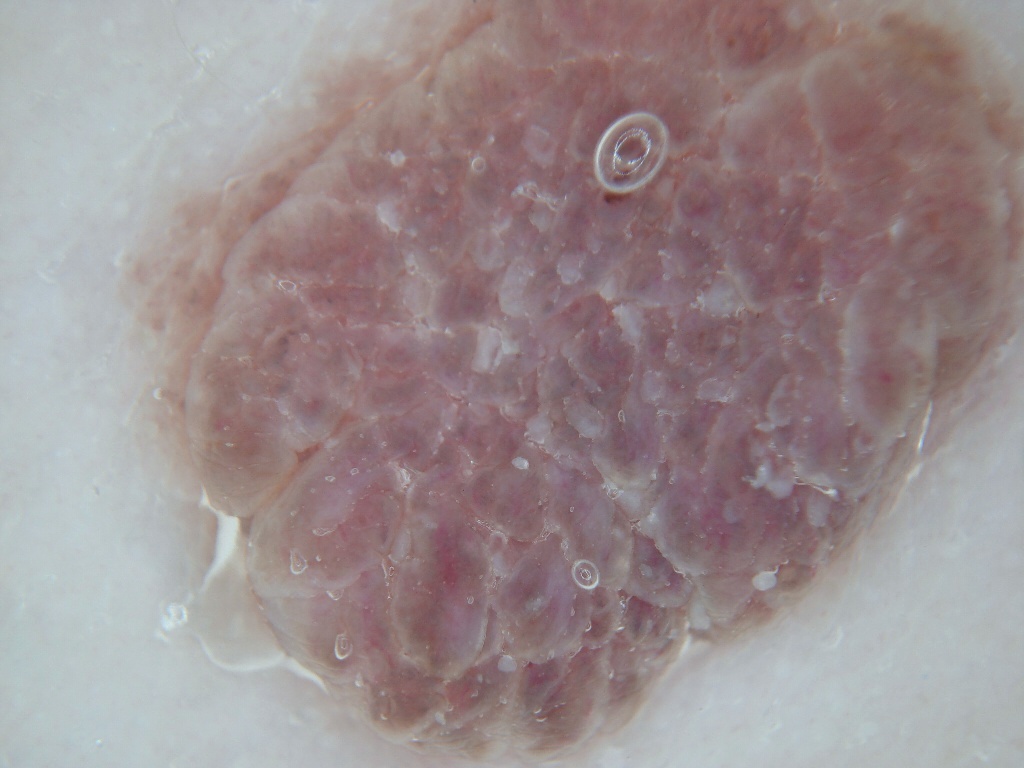A dermatoscopic image of a skin lesion. A female patient aged around 35. Dermoscopically, the lesion shows milia-like cysts, with no negative network, pigment network, or streaks. In (x1, y1, x2, y2) order, the lesion occupies the region <box>137, 1, 1021, 764</box>. Clinically diagnosed as a melanocytic nevus.